A dermatoscopic image of a skin lesion.
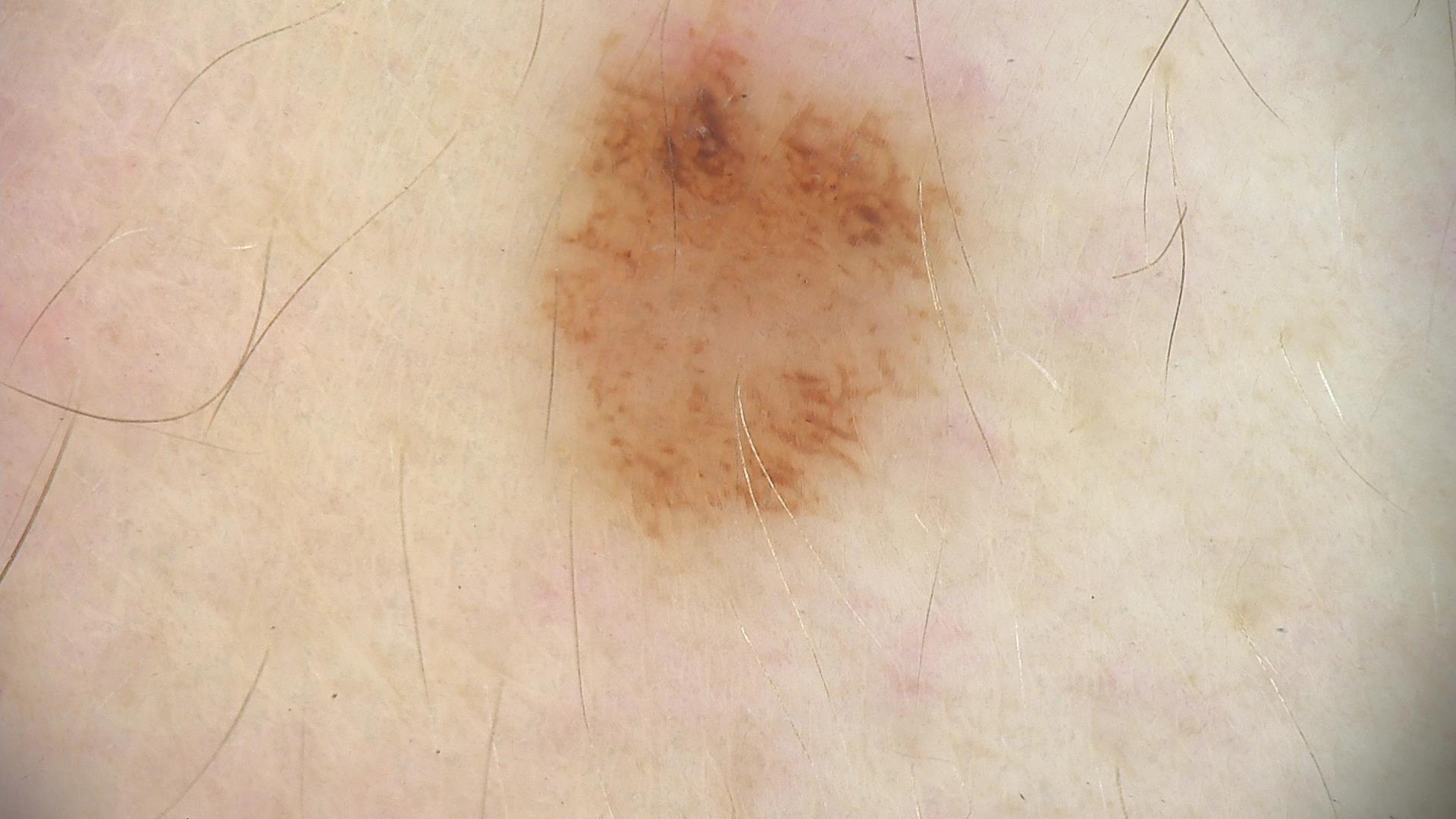• assessment: dysplastic junctional nevus (expert consensus)